The photo was captured at an angle — 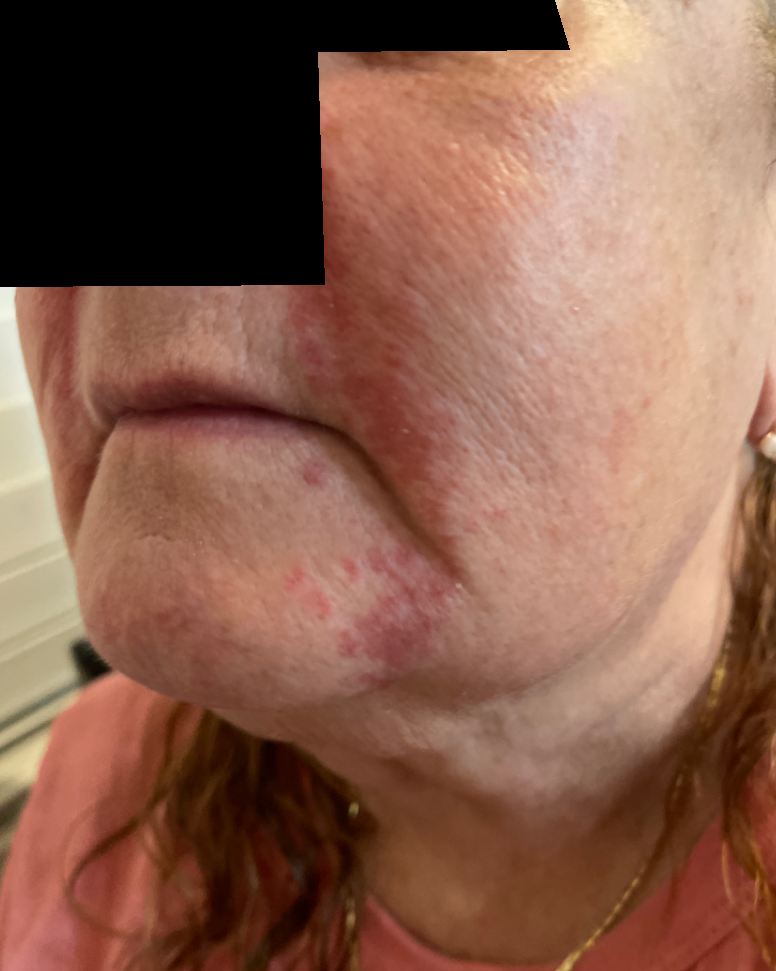Fitzpatrick skin type II.
Reviewed remotely by one dermatologist: favoring Perioral Dermatitis; possibly Rosacea.